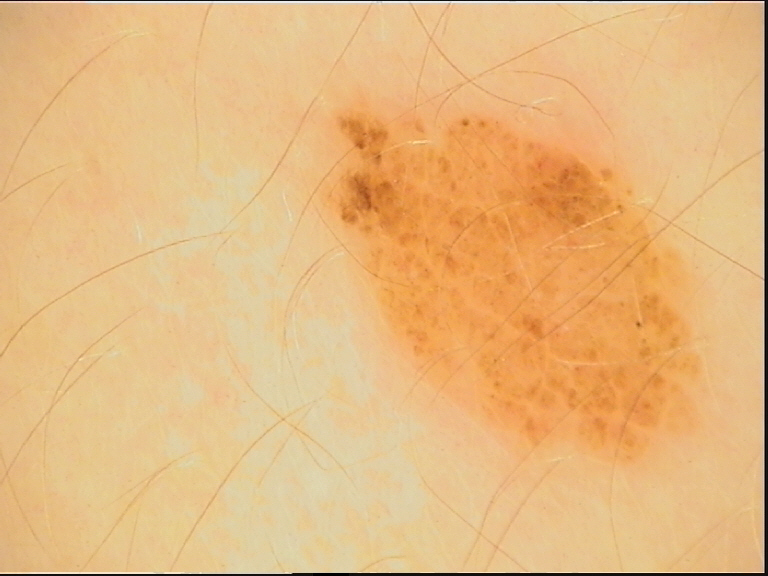Summary:
The morphology is that of a banal lesion.
Conclusion:
The diagnosis was a compound nevus.